A dermoscopy image of a single skin lesion.
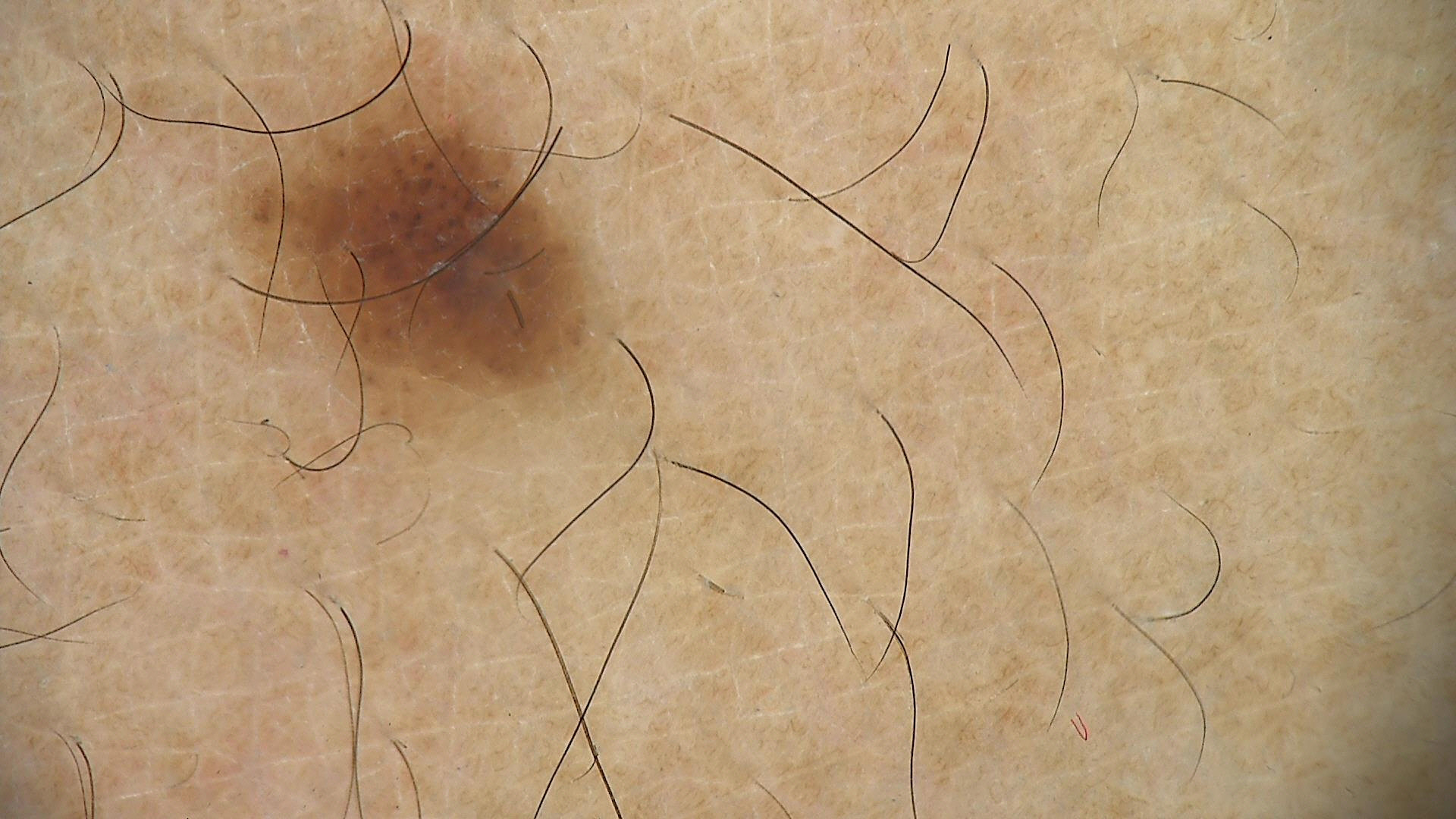{
  "diagnosis": {
    "name": "dysplastic compound nevus",
    "code": "cd",
    "malignancy": "benign",
    "super_class": "melanocytic",
    "confirmation": "expert consensus"
  }
}